A dermoscopic photograph of a skin lesion; a female subject roughly 35 years of age.
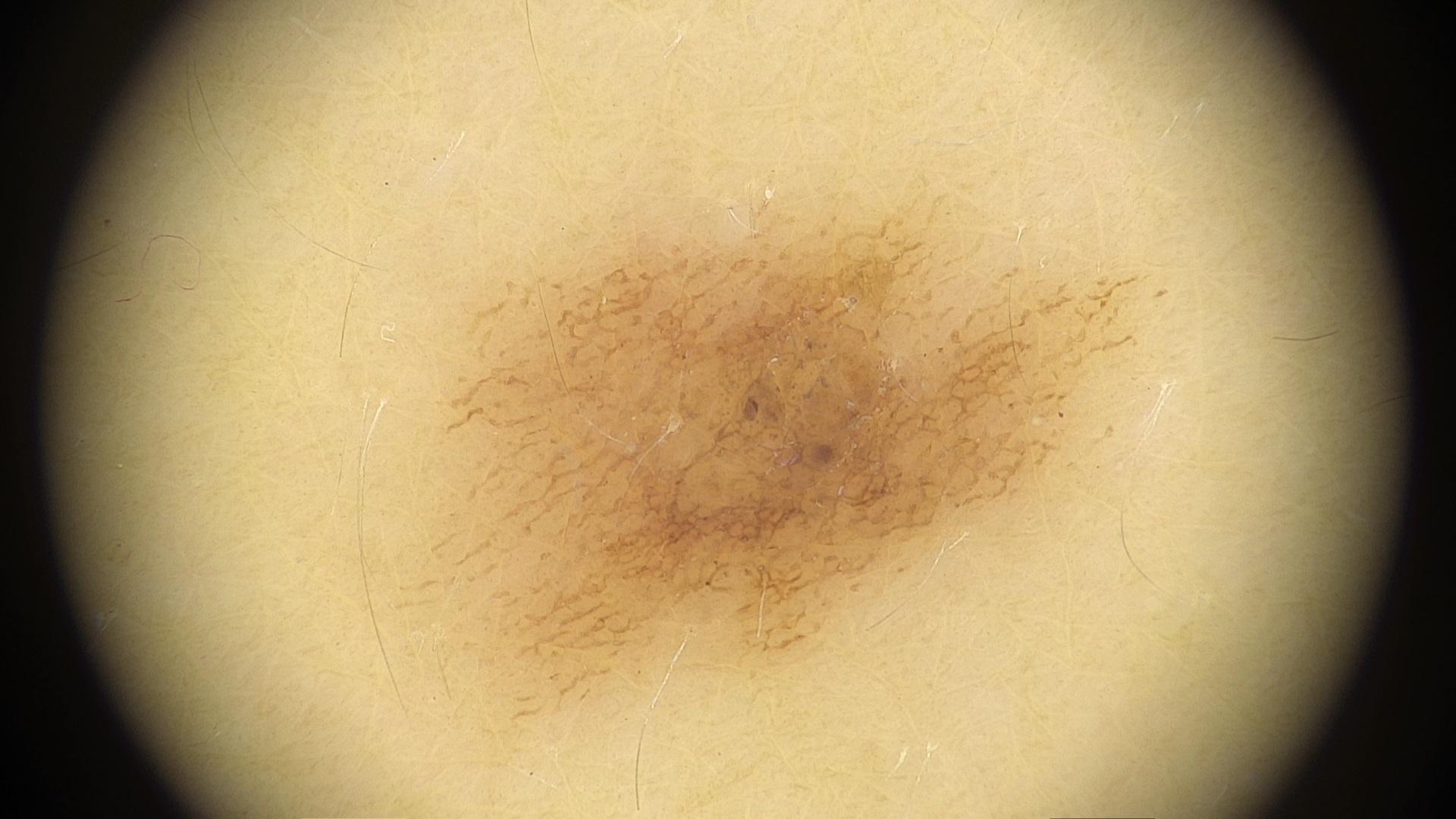Impression:
Expert review favored a benign lesion — a nevus.